A dermoscopic close-up of a skin lesion.
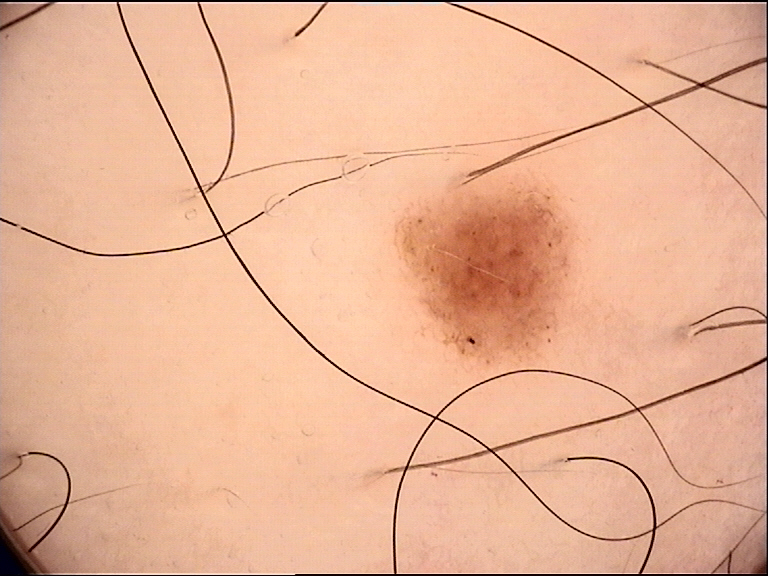Conclusion:
Labeled as a dysplastic junctional nevus.